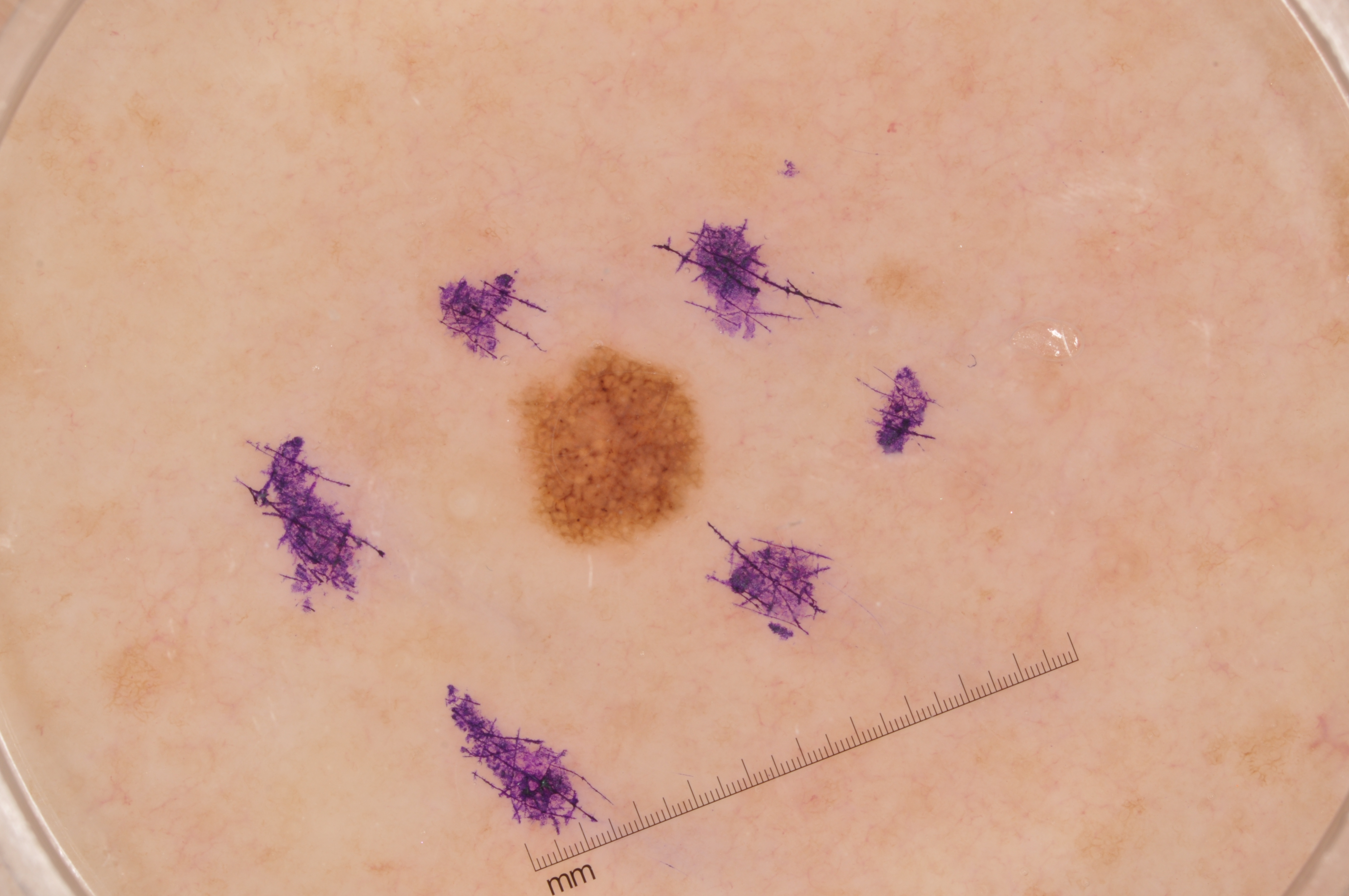Case summary:
• imaging · dermoscopic image
• lesion extent · ~2% of the field
• dermoscopic findings · pigment network
• lesion bbox · (527, 350, 706, 546)
• impression · a melanocytic nevus